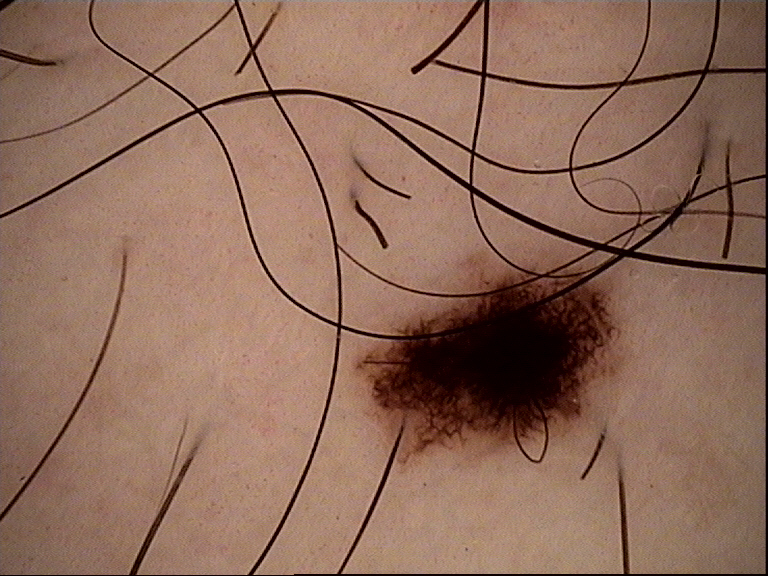Consistent with a dysplastic junctional nevus.